Male subject, age 30–39; close-up view: 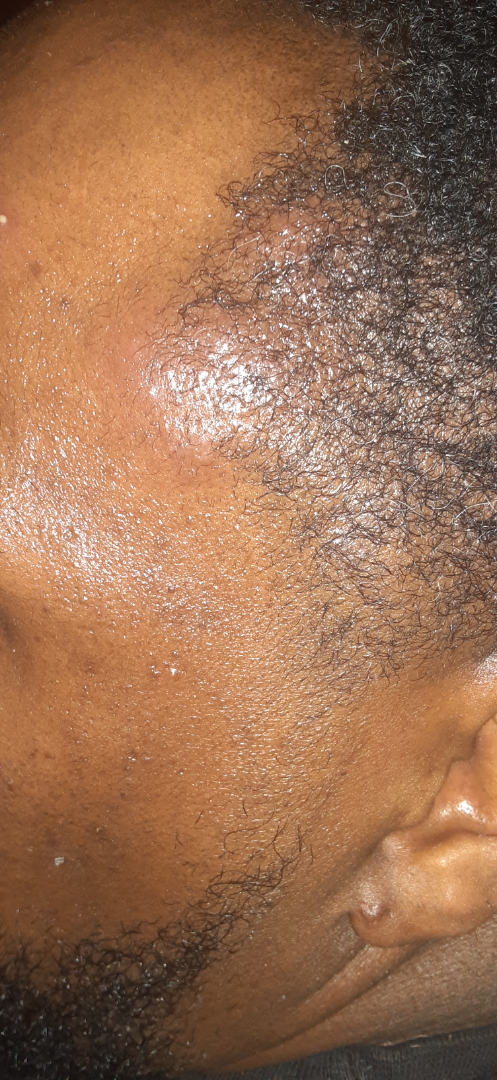Review: On photographic review, Pemphigus vulgaris (considered); Acne (considered).